The photograph is a close-up of the affected area; the patient is 60–69, female; the affected area is the leg: 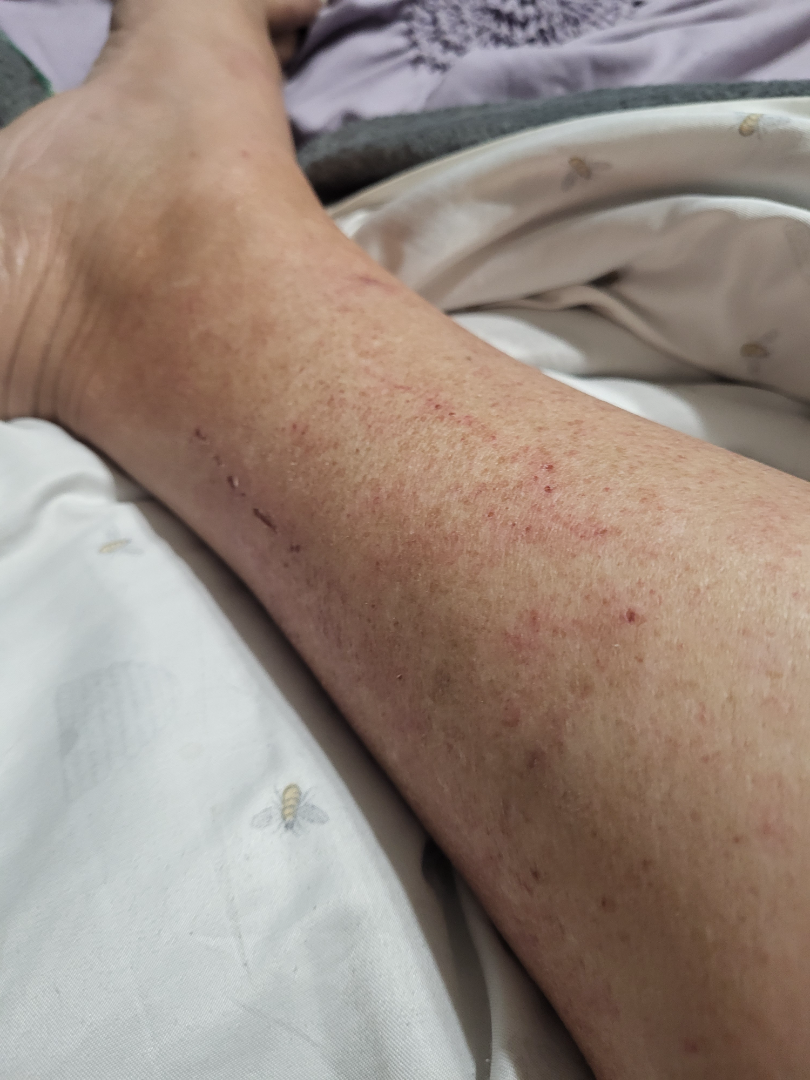Case summary:
* differential diagnosis: favoring Stasis Dermatitis; with consideration of Allergic Contact Dermatitis; an alternative is Pigmented purpuric eruption